A dermoscopic image of a skin lesion.
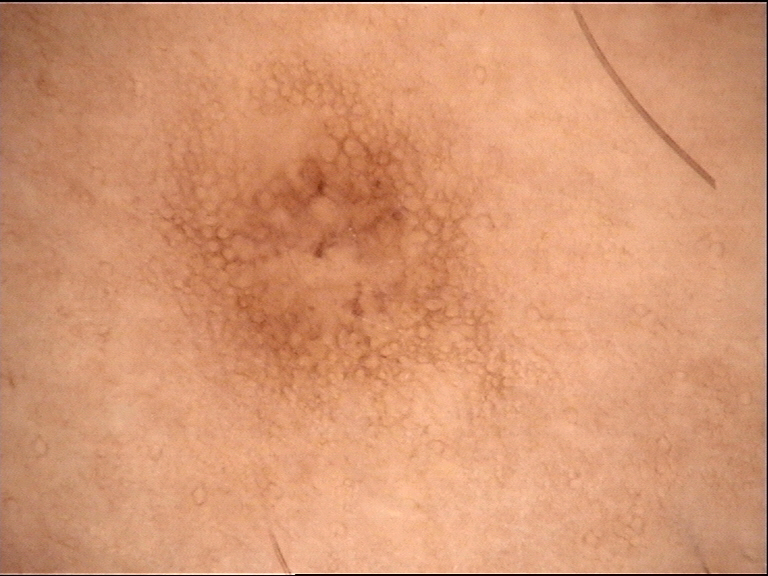Q: What kind of lesion is this?
A: banal
Q: What is the diagnosis?
A: junctional nevus (expert consensus)